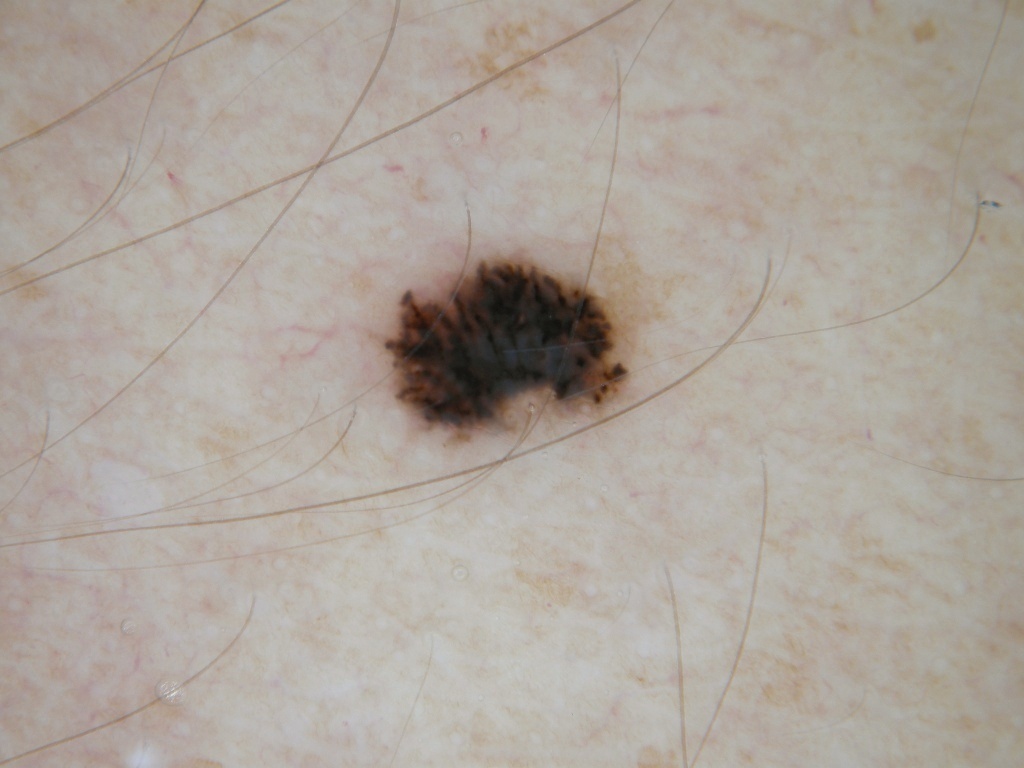A female subject roughly 20 years of age. A dermatoscopic image of a skin lesion. Dermoscopic review identifies no pigment network, streaks, globules, negative network, or milia-like cysts. A small lesion occupying a minor part of the field. With coordinates (x1, y1, x2, y2), the lesion is bounded by <bbox>381, 253, 637, 446</bbox>. The diagnostic assessment was a melanocytic nevus.